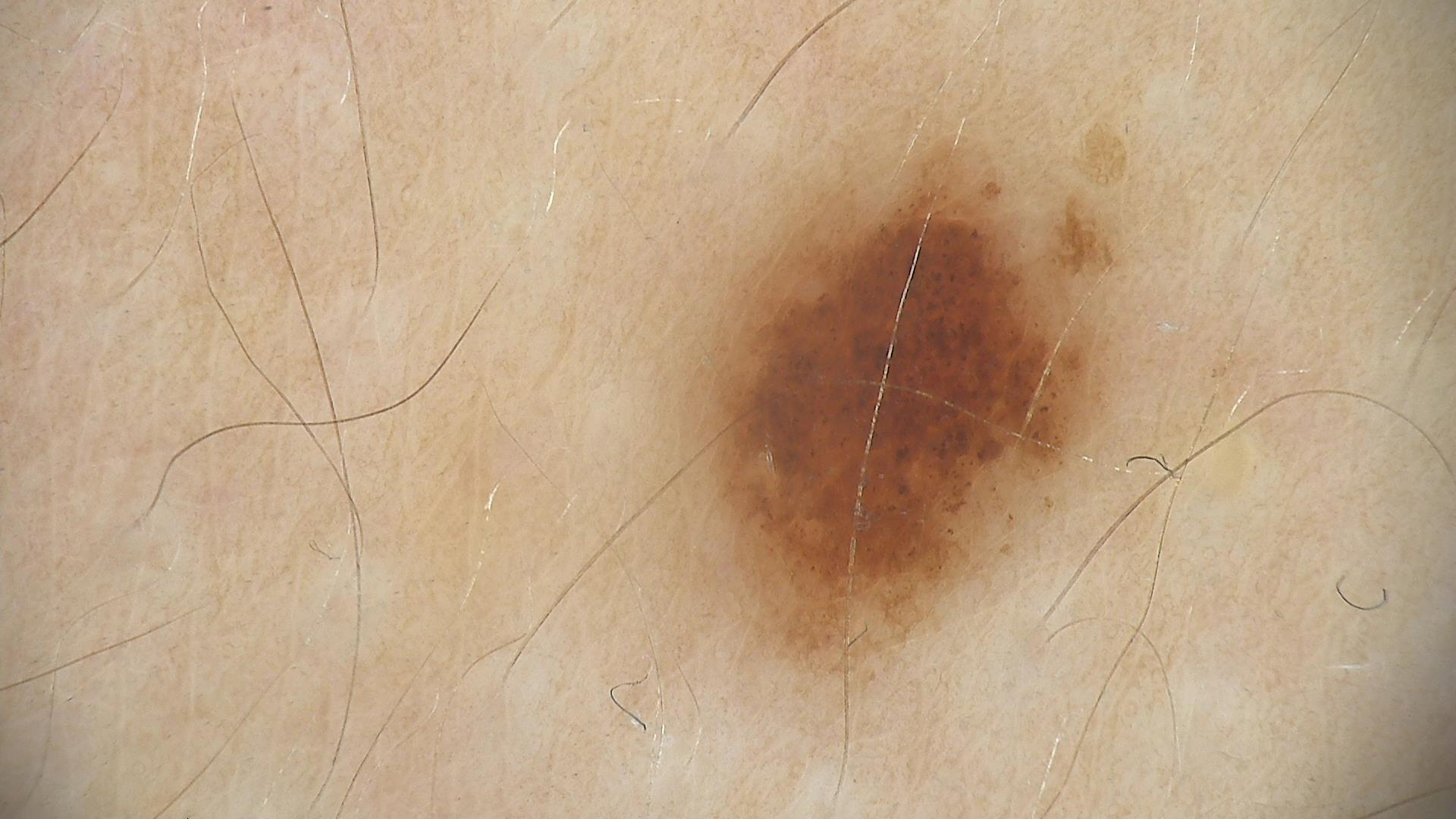Conclusion:
The diagnosis was a banal lesion — a compound nevus.